The affected area is the arm; texture is reported as raised or bumpy; the patient considered this a rash; this is a close-up image; the patient reports itching; the condition has been present for one to four weeks:
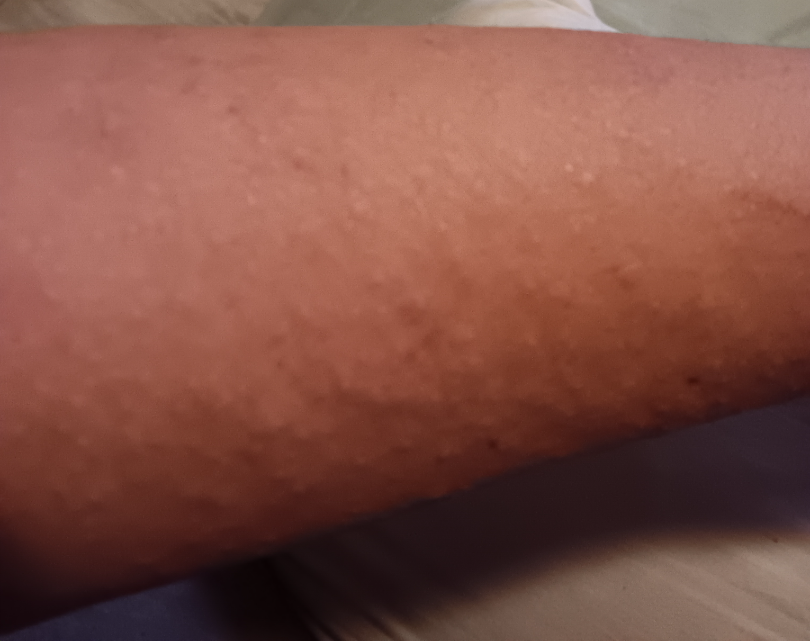assessment: could not be assessed